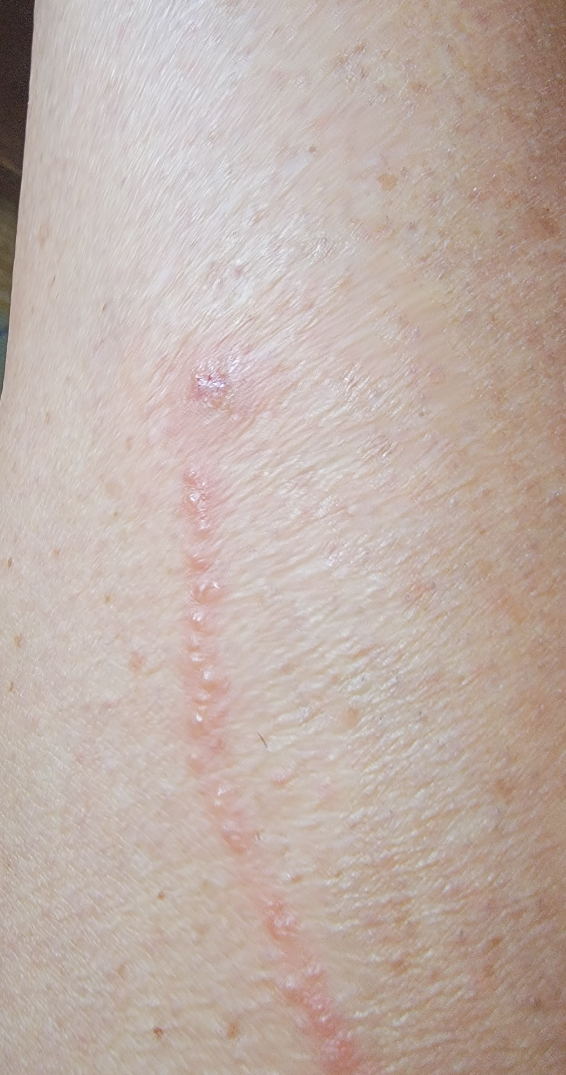Q: Duration?
A: about one day
Q: Where on the body?
A: leg
Q: Fitzpatrick or Monk tone?
A: Fitzpatrick II
Q: Who is the patient?
A: female, age 60–69
Q: How was the photo taken?
A: close-up
Q: Reported symptoms?
A: itching and bothersome appearance
Q: What is the dermatologist's impression?
A: favoring Lichen striatus; the differential also includes Herpes Zoster; possibly Allergic Contact Dermatitis